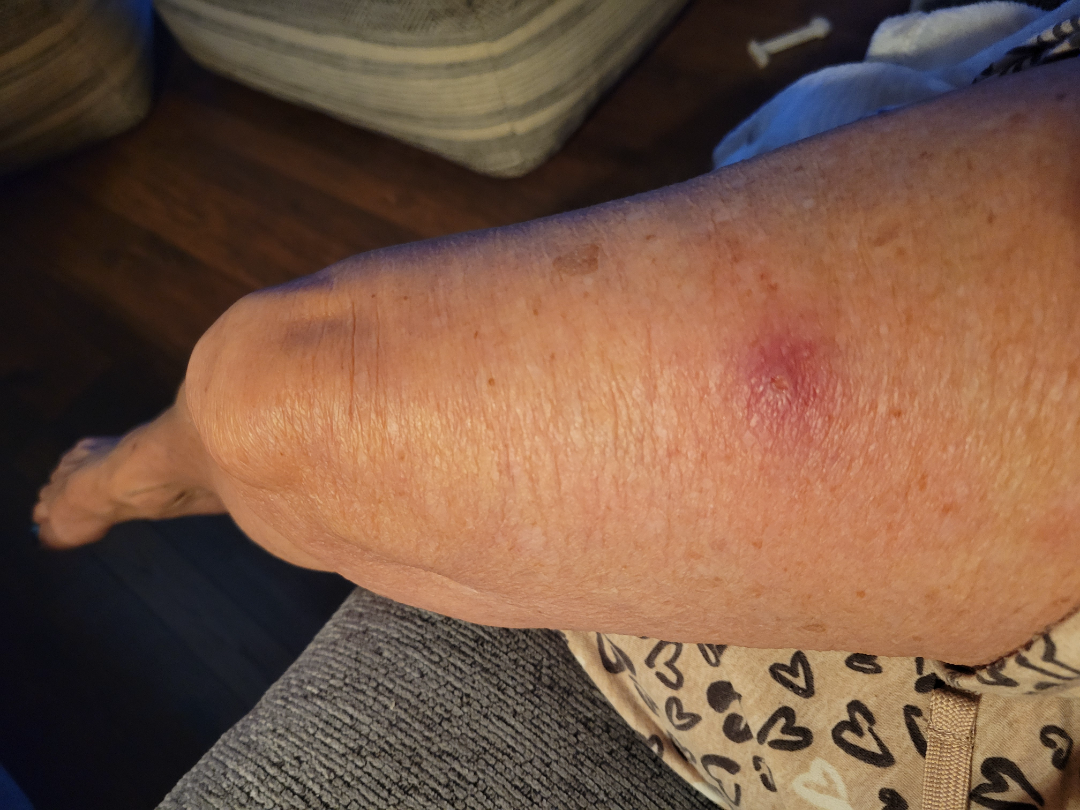<report>
  <shot_type>at a distance</shot_type>
  <symptoms>darkening, bothersome appearance, pain, enlargement, bleeding</symptoms>
  <body_site>leg</body_site>
  <texture>fluid-filled, raised or bumpy</texture>
  <patient>female, age 70–79</patient>
  <systemic_symptoms>none reported</systemic_symptoms>
  <differential>
    <tied_lead>Abscess, Insect Bite</tied_lead>
    <unlikely>SCC/SCCIS</unlikely>
  </differential>
</report>